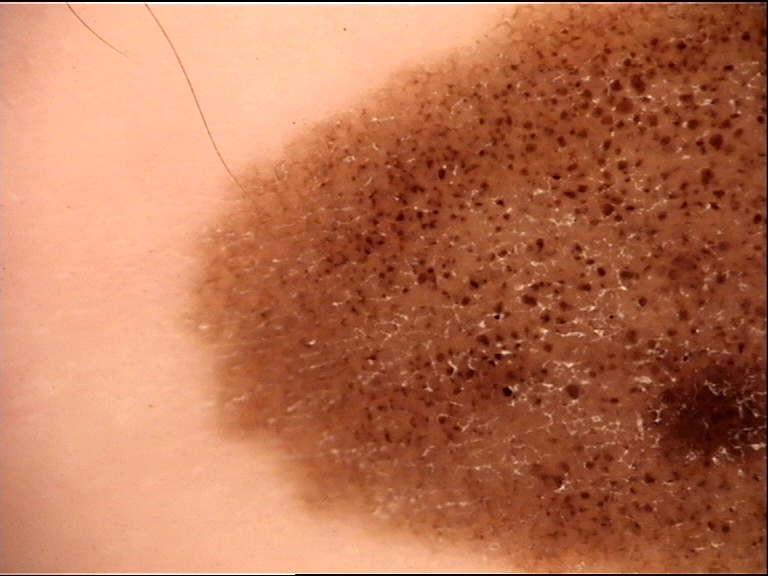A dermatoscopic image of a skin lesion. This is a banal lesion. Labeled as a congenital compound nevus.